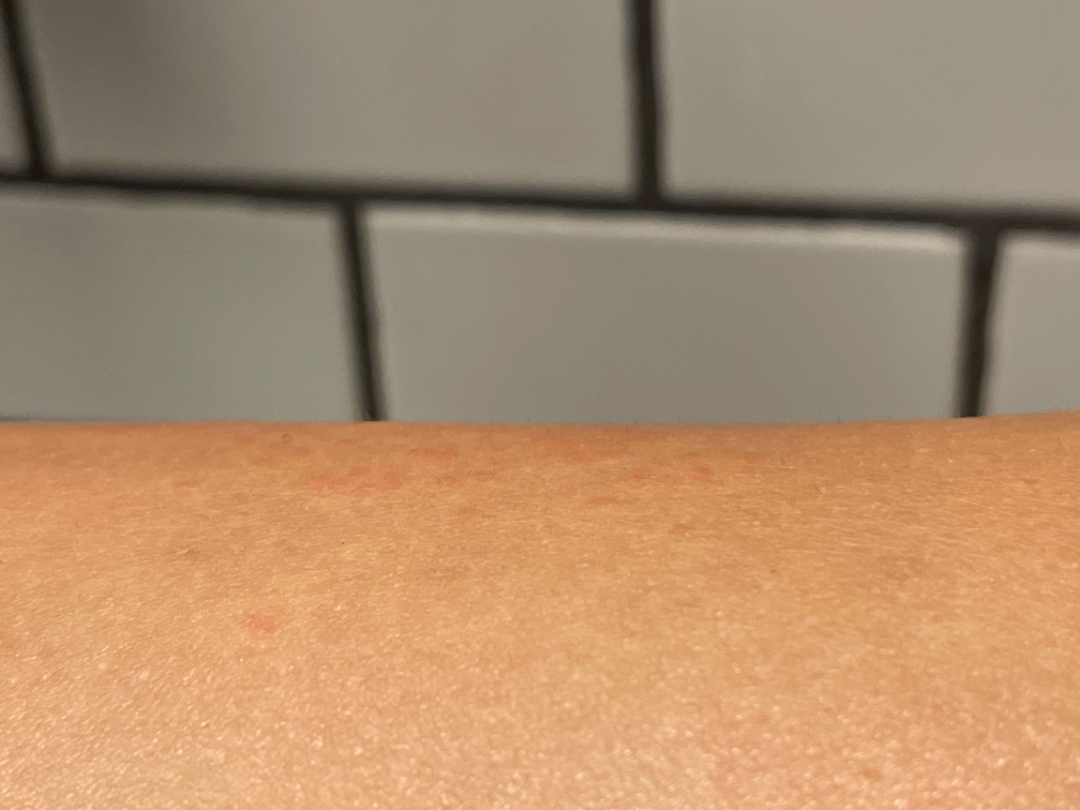Clinical context: The contributor is female. The patient described the issue as a rash. The photograph was taken at an angle. Present for about one day. The lesion involves the leg. Assessment: On teledermatology review, the differential is split between Eczema and Allergic Contact Dermatitis.